A dermoscopic close-up of a skin lesion.
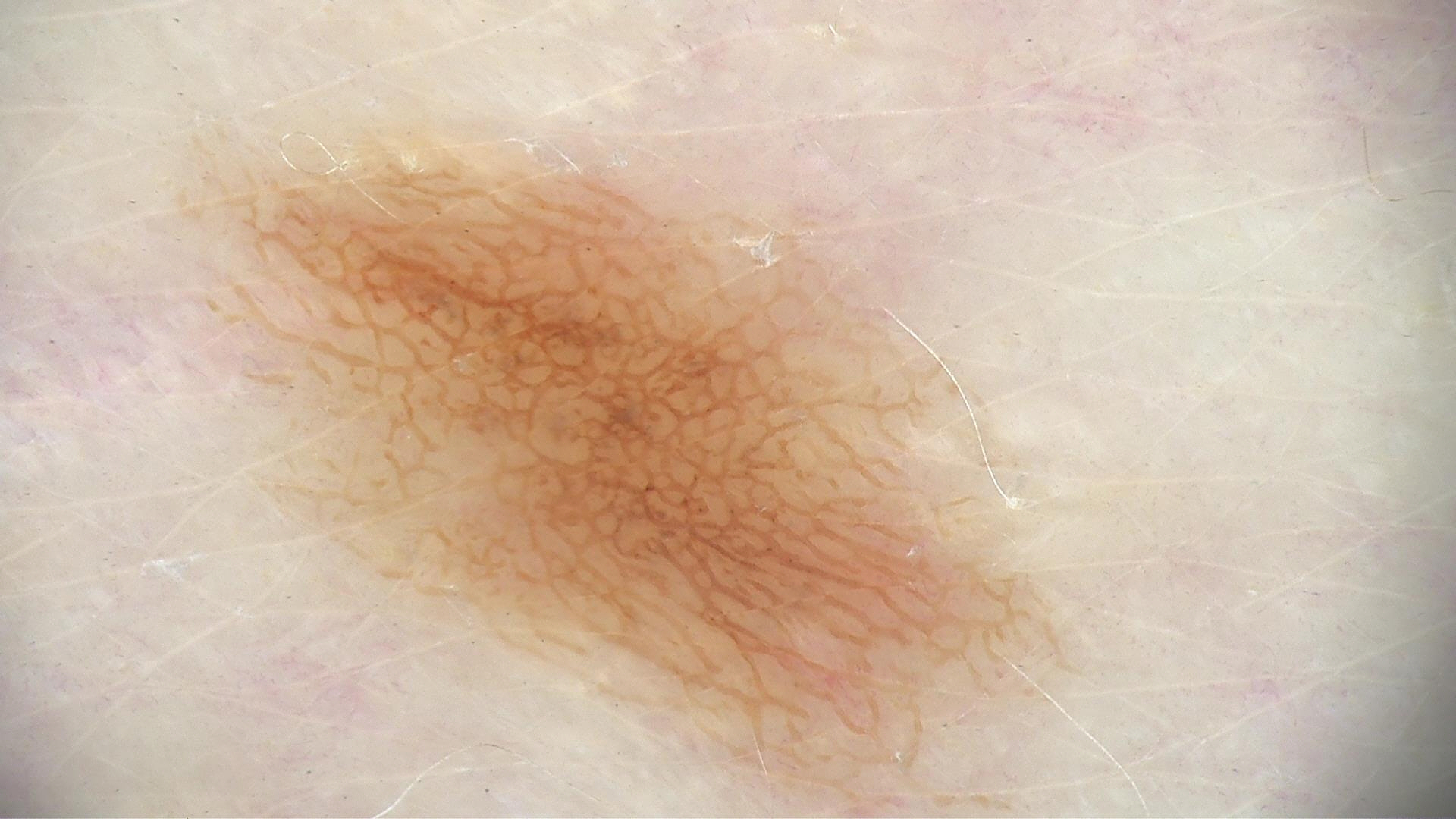Impression:
The diagnostic label was a dysplastic junctional nevus.